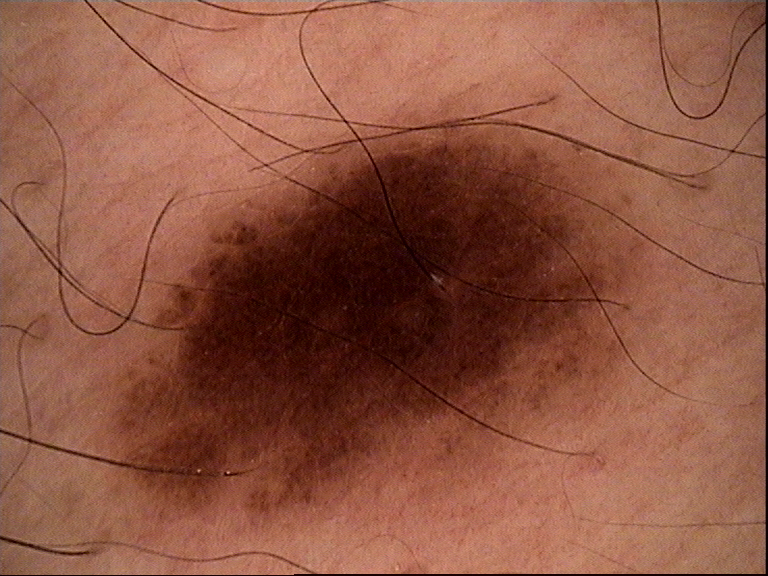{
  "image": "dermoscopy",
  "diagnosis": {
    "name": "dysplastic junctional nevus",
    "code": "jd",
    "malignancy": "benign",
    "super_class": "melanocytic",
    "confirmation": "expert consensus"
  }
}